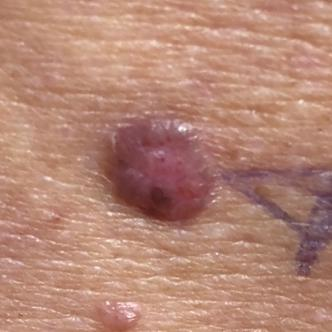  diagnosis:
    name: basal cell carcinoma
    code: BCC
    malignancy: malignant
    confirmation: histopathology